Dermoscopy of a skin lesion:
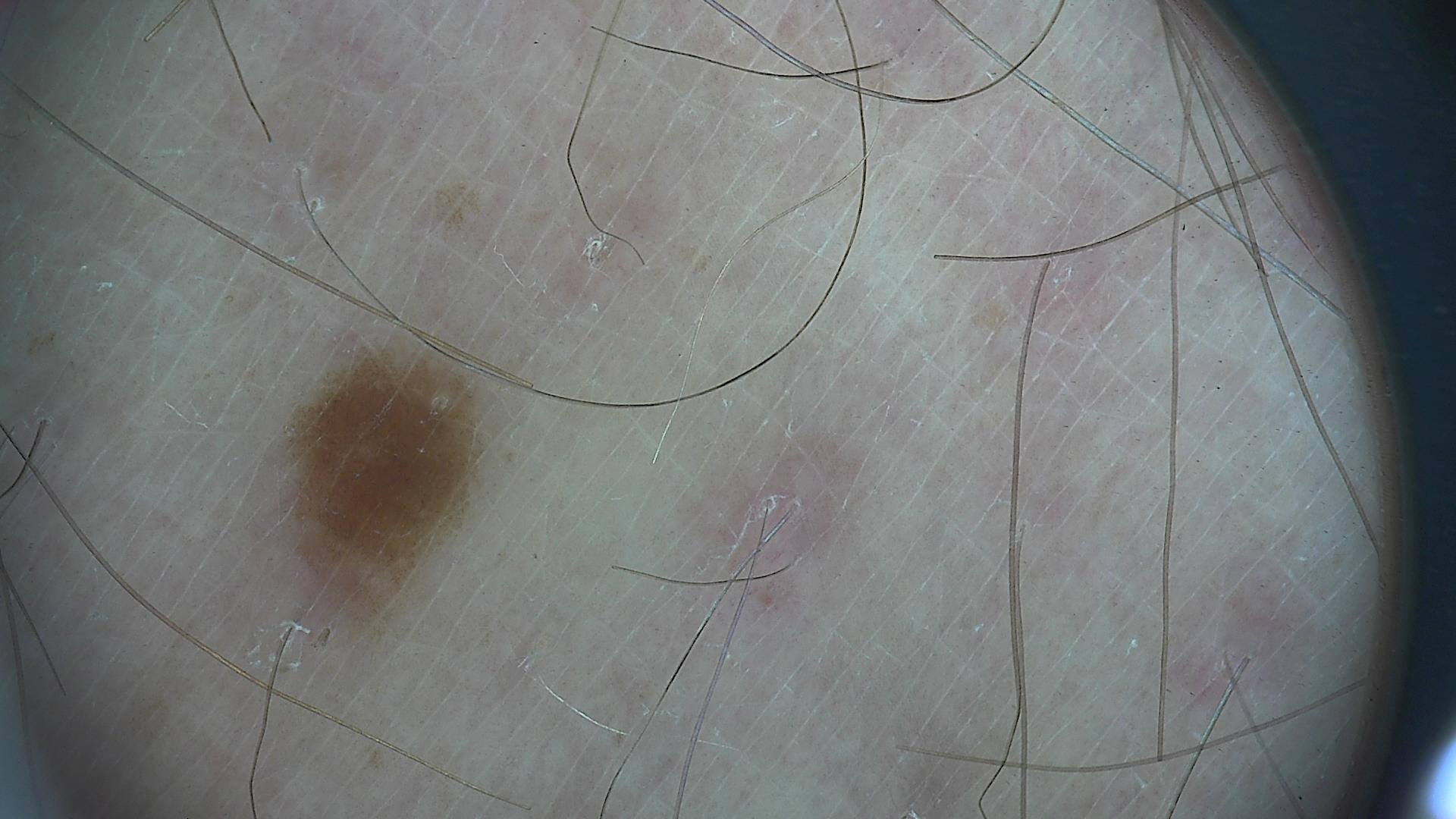The diagnosis was a banal lesion — a junctional nevus.